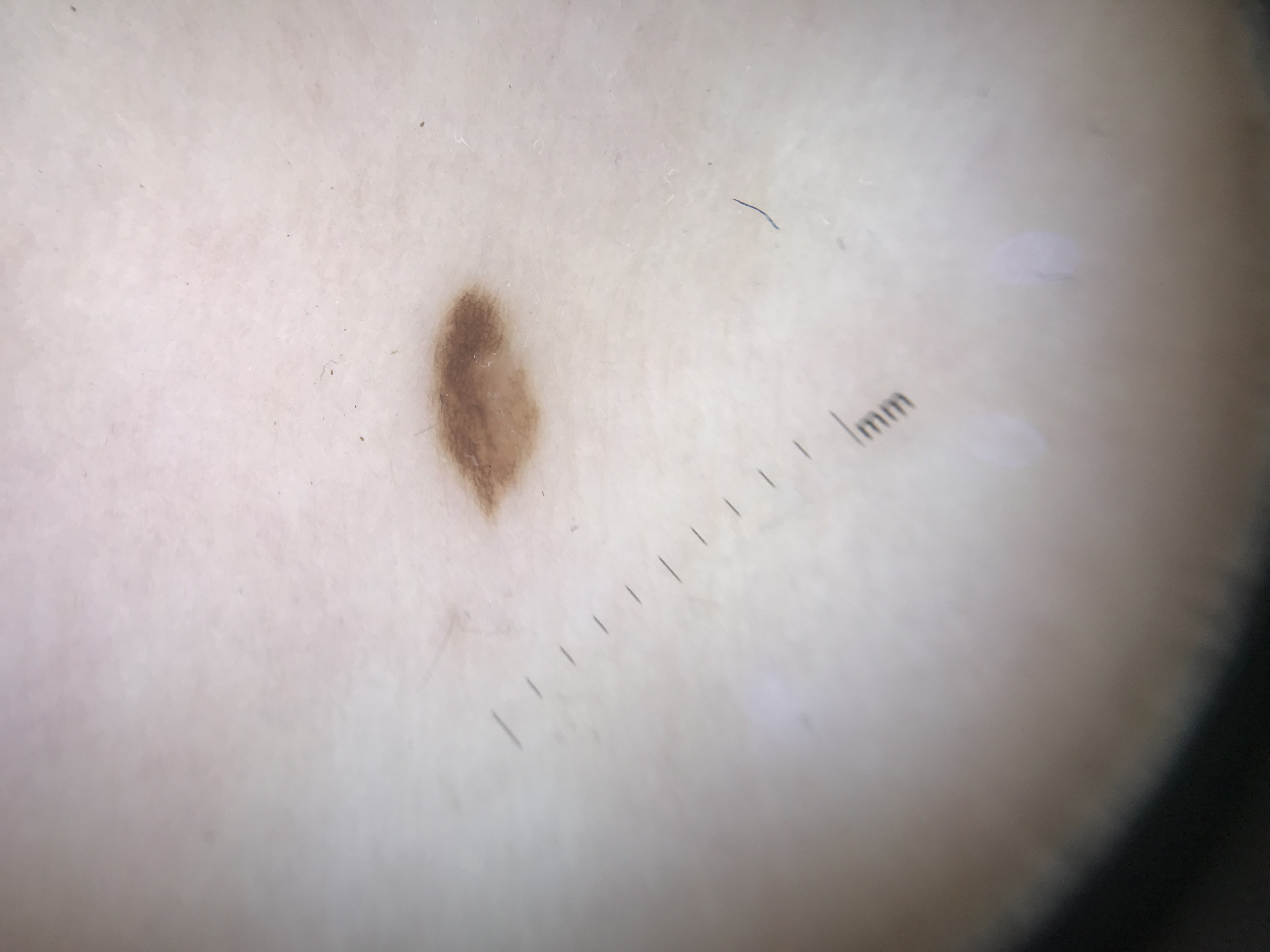Findings: A skin lesion imaged with a dermatoscope. Conclusion: Classified as a benign lesion — a dysplastic junctional nevus.